Dermoscopy of a skin lesion:
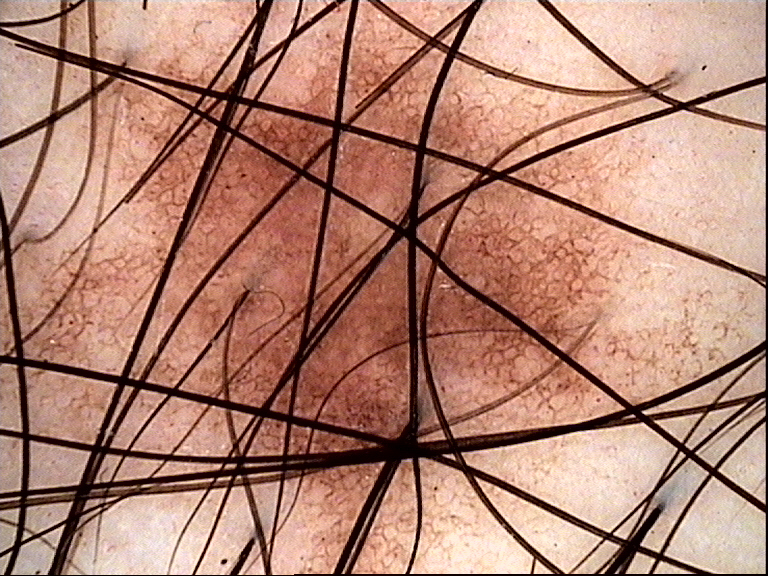The diagnosis was a benign lesion — a dysplastic junctional nevus.